The photo was captured at an angle: 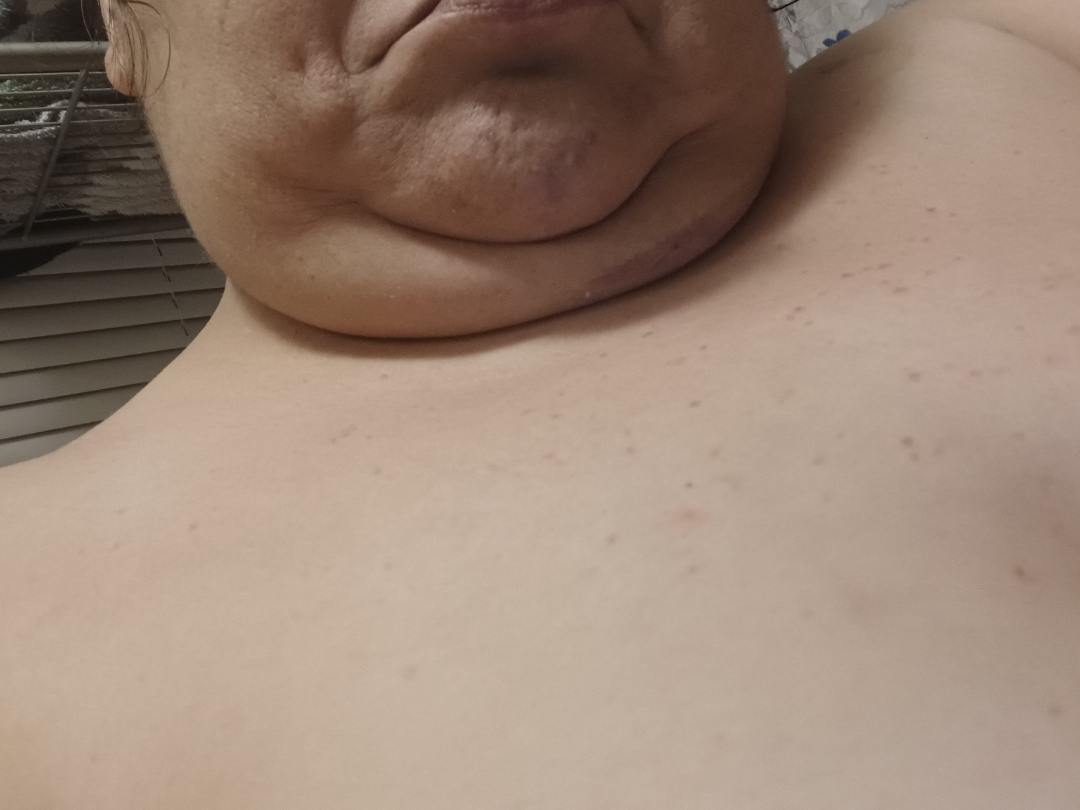| feature | finding |
|---|---|
| assessment | ungradable on photographic review |